A smartphone photograph of a skin lesion. A male patient in their 60s: 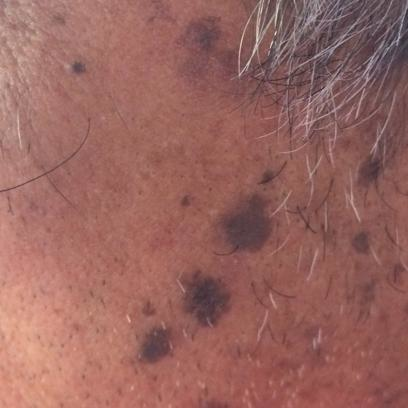site = the face; patient-reported symptoms = elevation, growth / no itching, no bleeding; diagnosis = seborrheic keratosis (clinical consensus).